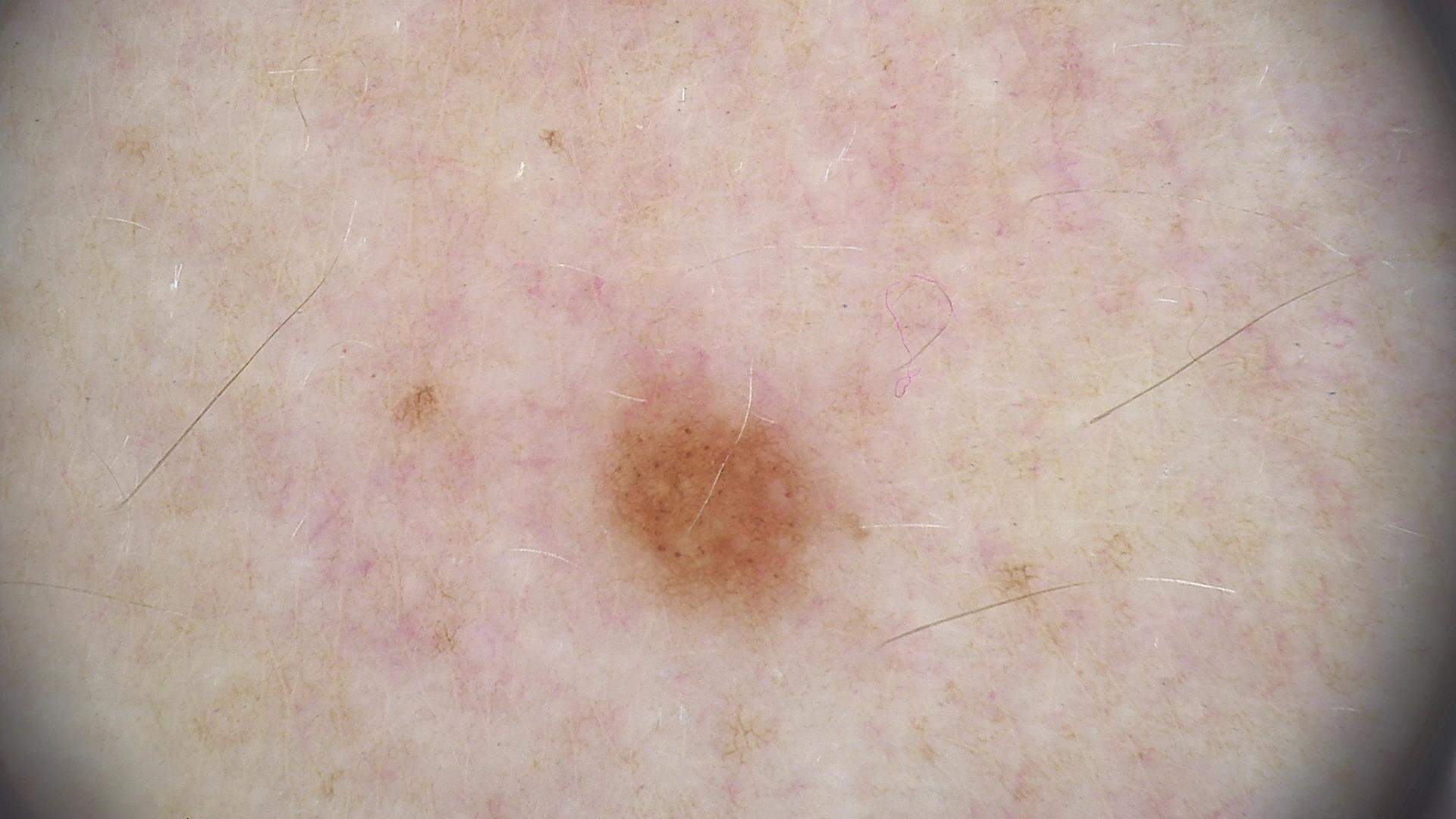| field | value |
|---|---|
| label | dysplastic junctional nevus (expert consensus) |